The lesion involves the back of the hand. A close-up photograph: 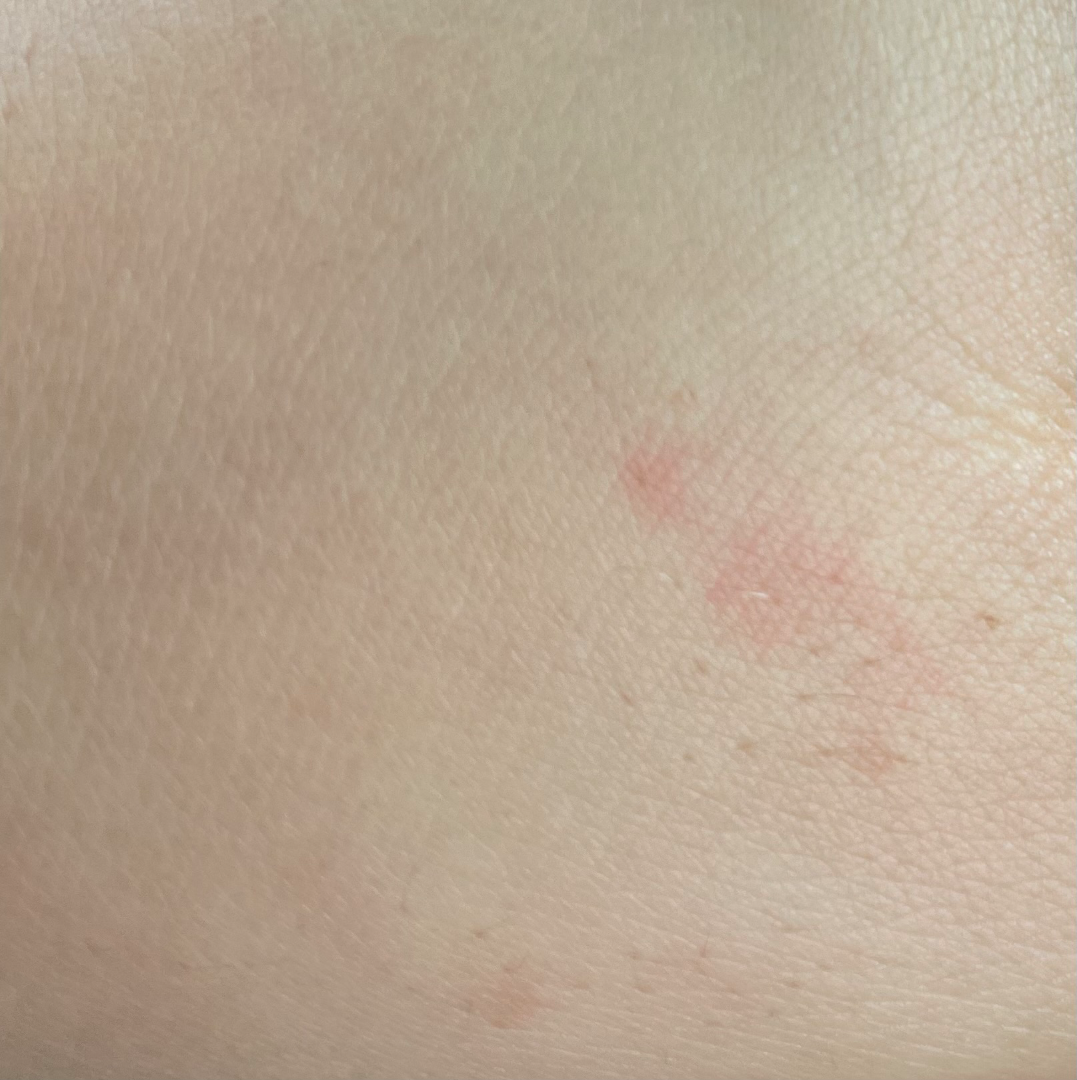assessment: ungradable on photographic review
systemic_symptoms: fatigue
skin_tone:
  fitzpatrick: II
  monk_skin_tone: 1
texture: flat
duration: about one day
symptoms: bothersome appearance